Dermoscopy of a skin lesion: 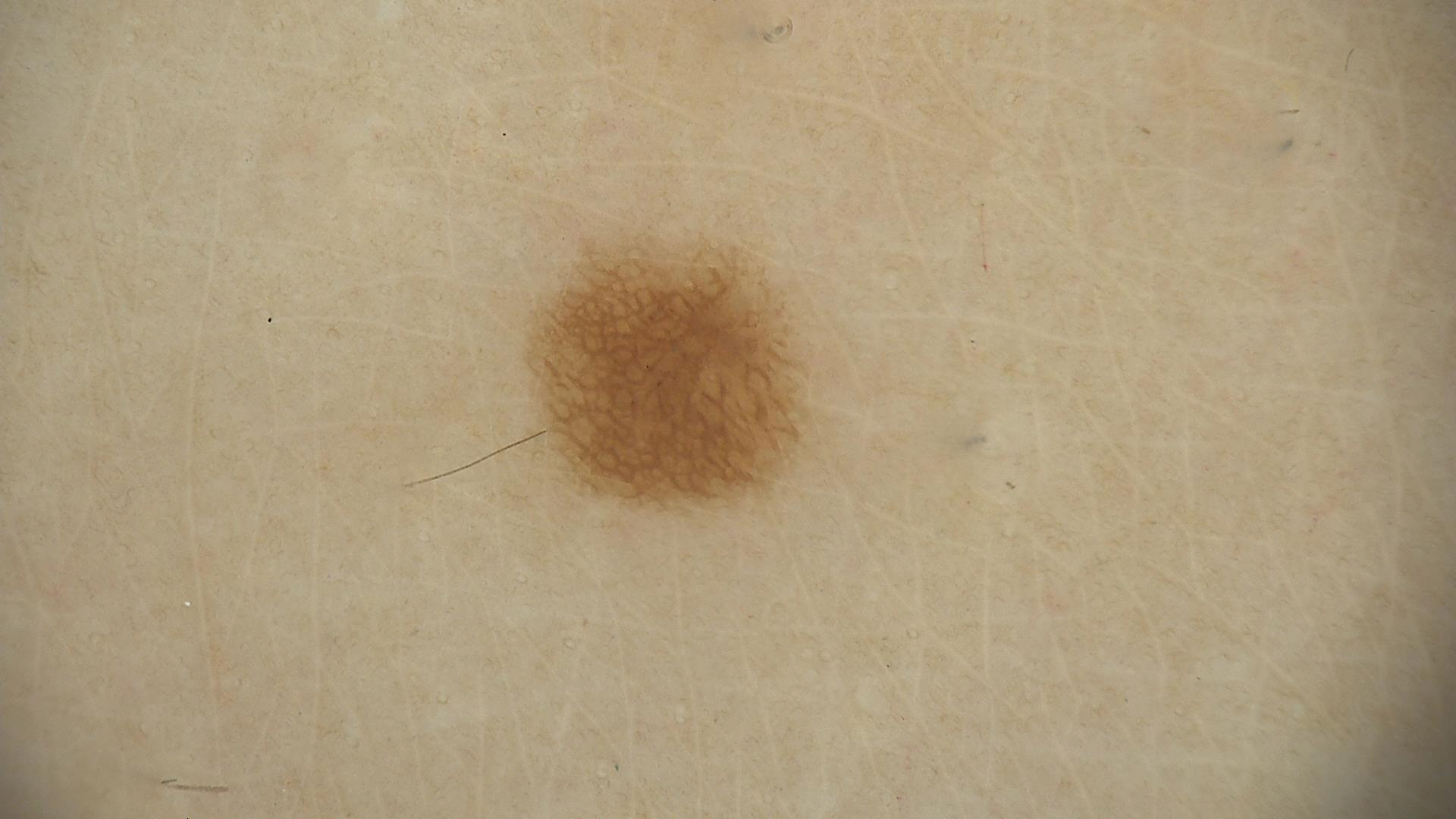Conclusion:
Diagnosed as a banal lesion — a junctional nevus.